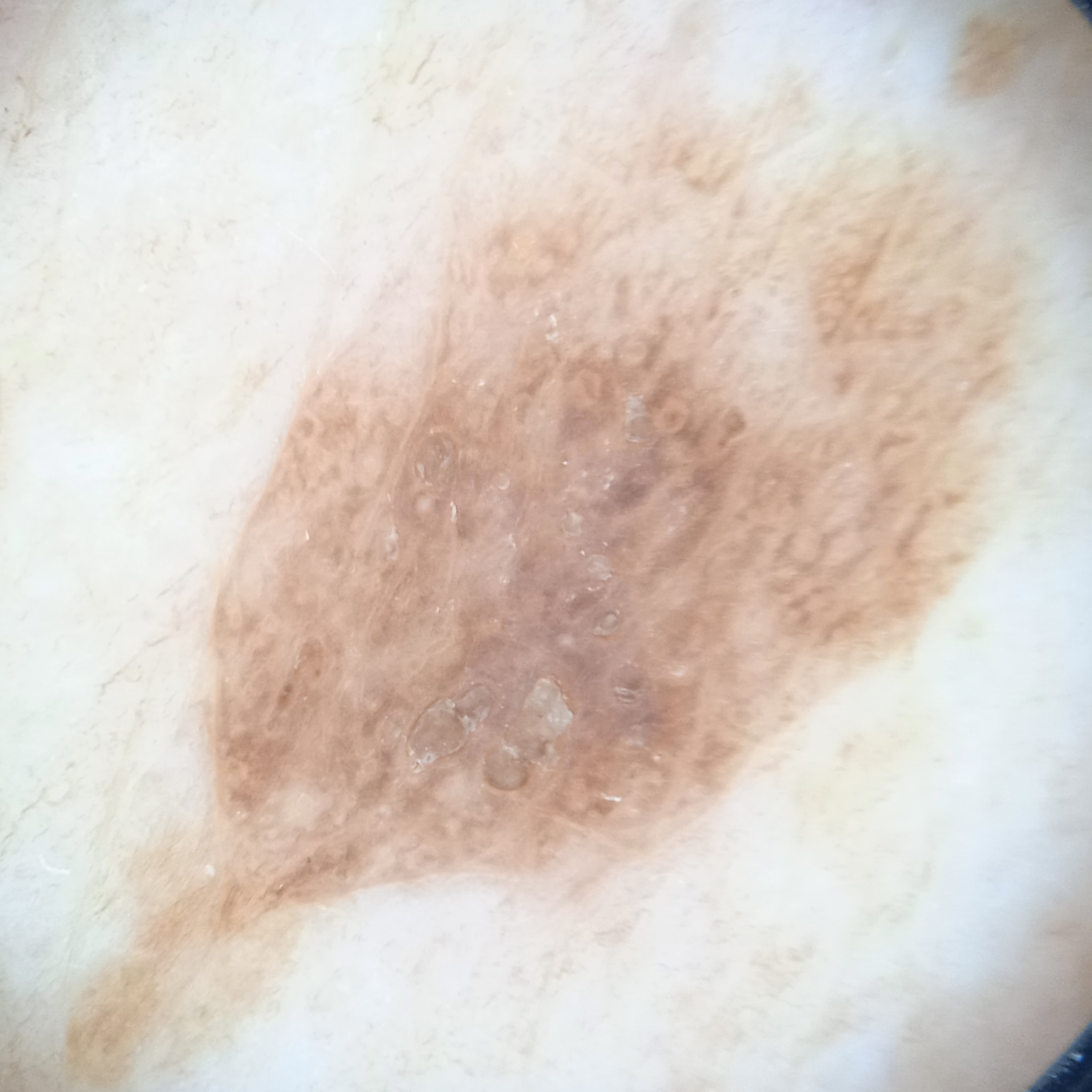{
  "sun_reaction": "skin reddens painfully with sun exposure",
  "referral": "research study (no referral diagnosis)",
  "mole_burden": "a moderate number of melanocytic nevi",
  "risk_factors": {
    "positive": [
      "a personal history of cancer",
      "immunosuppression",
      "a personal history of skin cancer"
    ],
    "negative": [
      "no family history of skin cancer"
    ]
  },
  "image": "dermoscopy",
  "lesion_location": "the back",
  "lesion_size": {
    "diameter_mm": 14.4
  },
  "diagnosis": {
    "name": "seborrheic keratosis",
    "malignancy": "benign"
  }
}